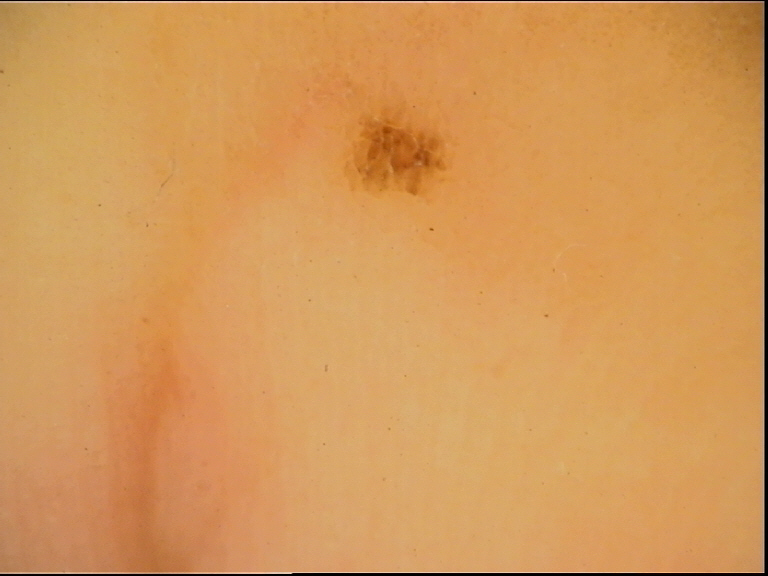imaging: dermoscopy, assessment: acral dysplastic junctional nevus (expert consensus).